A clinical close-up photograph of a skin lesion; a female patient aged 73 — 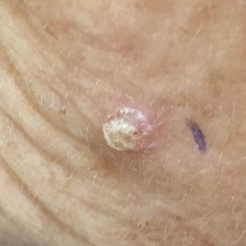Located on the face. The patient reports that the lesion is elevated and itches. Histopathologically confirmed as an actinic keratosis.